A dermatoscopic image of a skin lesion.
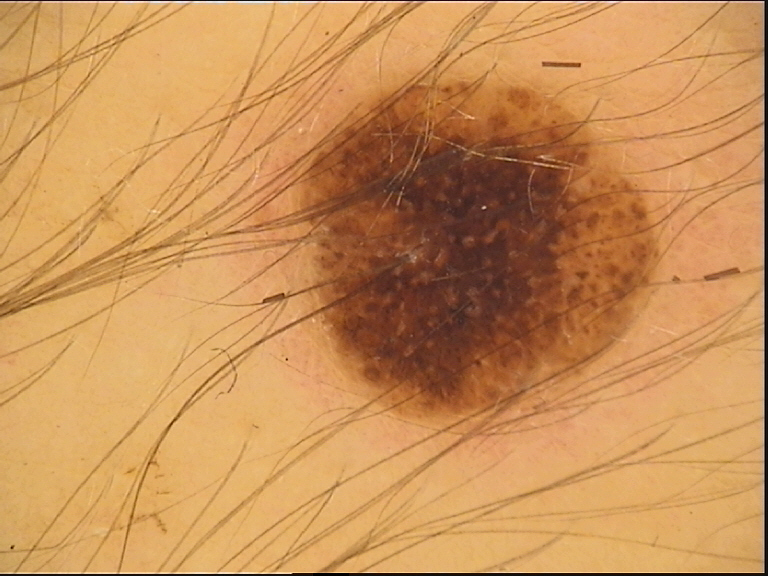subtype — banal; label — compound nevus (expert consensus).